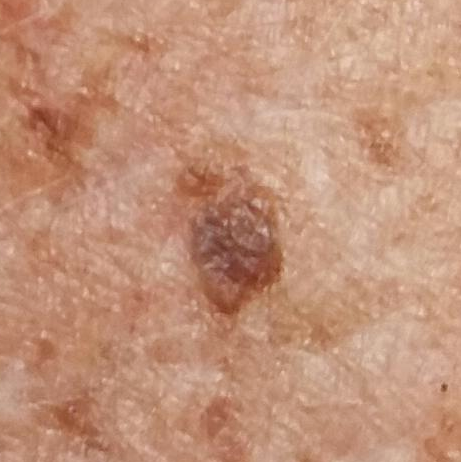– modality · clinical photo
– patient · in their 60s
– body site · the neck
– assessment · seborrheic keratosis (clinical consensus)